A dermoscopy image of a single skin lesion.
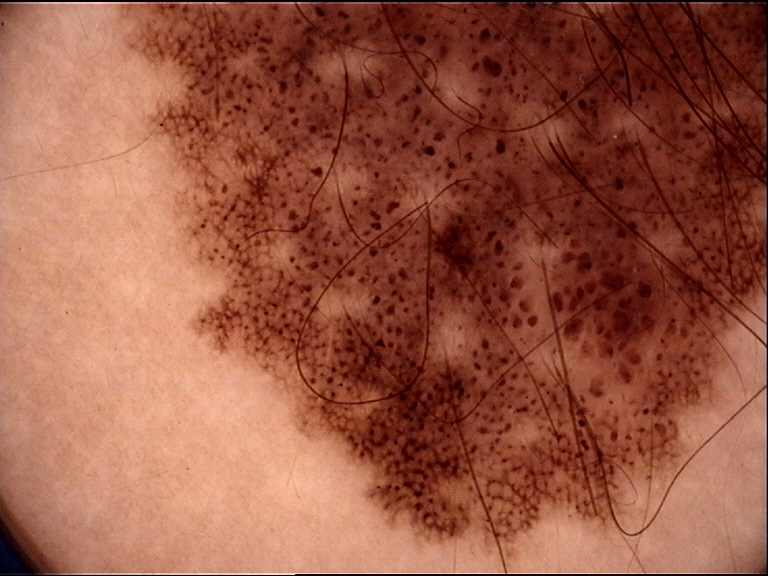Case: This is a banal lesion. Conclusion: Labeled as a congenital compound nevus.